The contributor is a female aged 50–59. Self-categorized by the patient as a rash. This image was taken at a distance. The patient also reports joint pain. Located on the front of the torso, back of the hand, palm, back of the torso and arm:
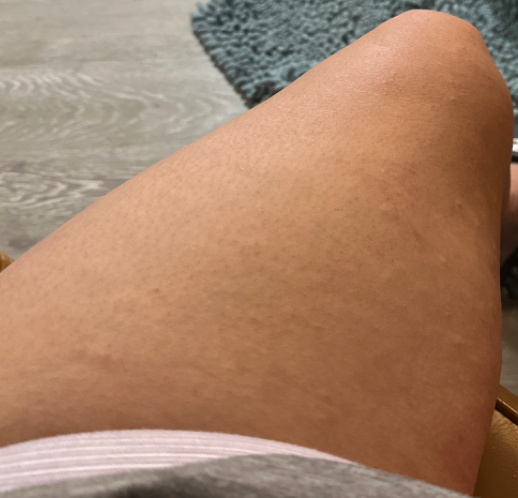{"differential": {"tied_lead": ["Allergic Contact Dermatitis", "Eczema"]}}